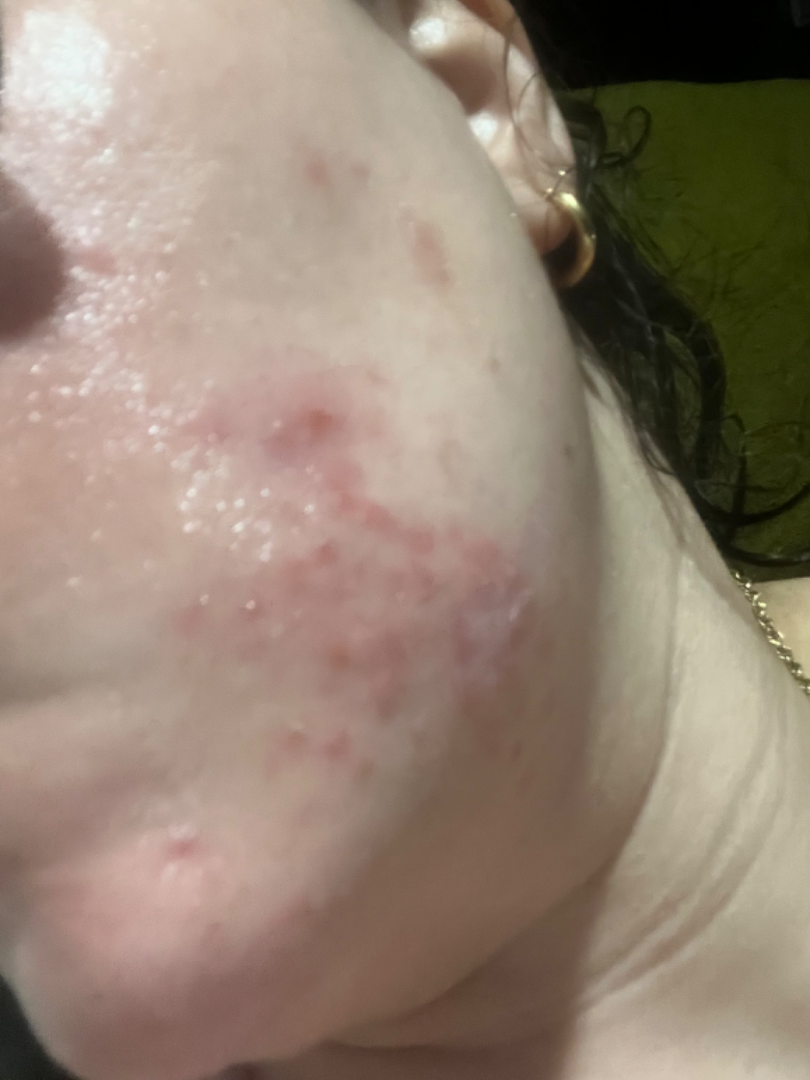This is a close-up image. The patient is 30–39, female. The differential includes Acne and Rosacea, with no clear leading consideration.